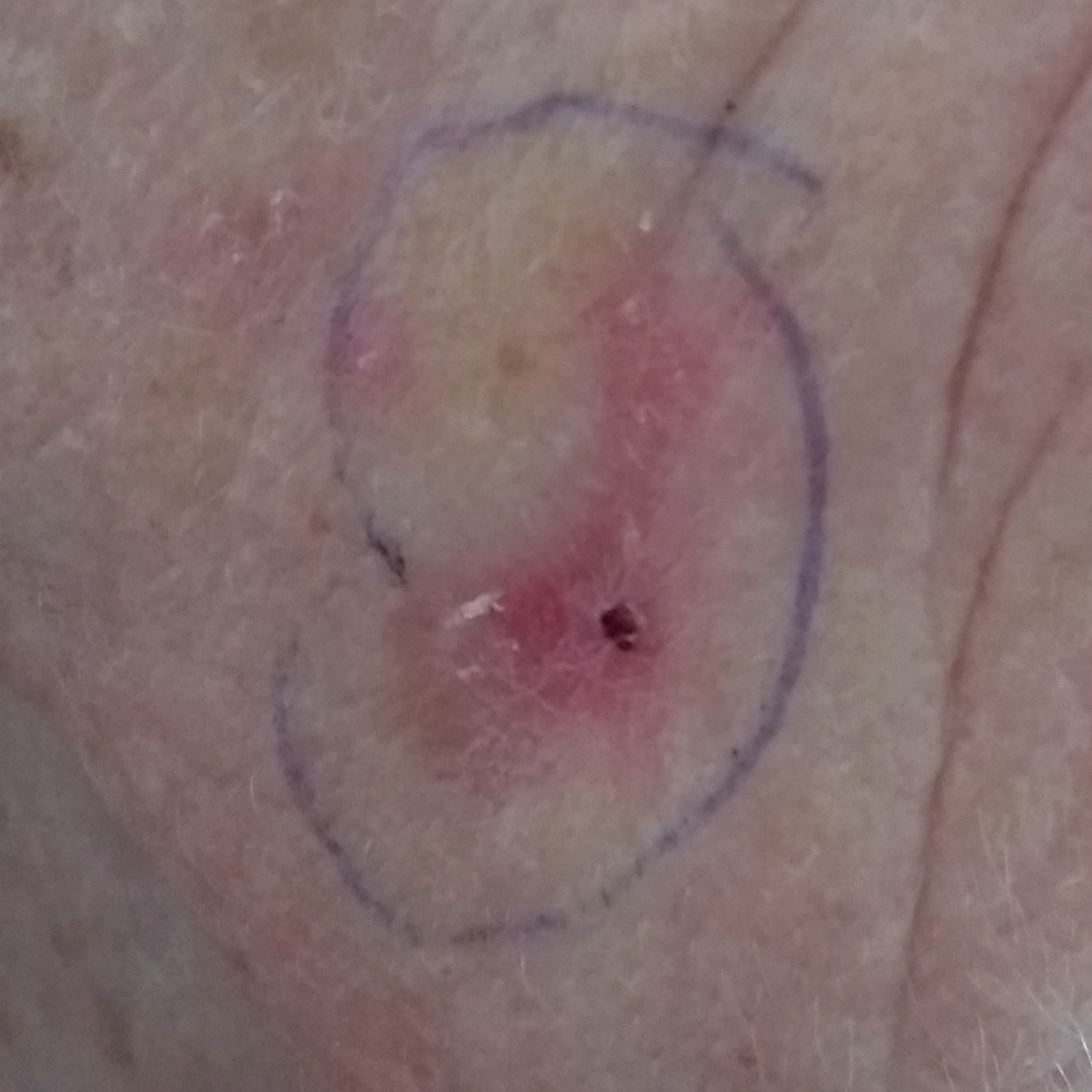image: clinical photograph | patient: female, 83 years of age | Fitzpatrick: II | anatomic site: the face | symptoms: bleeding, itching, growth, pain / no change in appearance, no elevation | diagnosis: basal cell carcinoma (biopsy-proven).